A male patient about 85 years old or older; dermoscopy of a skin lesion; recorded as skin type II:
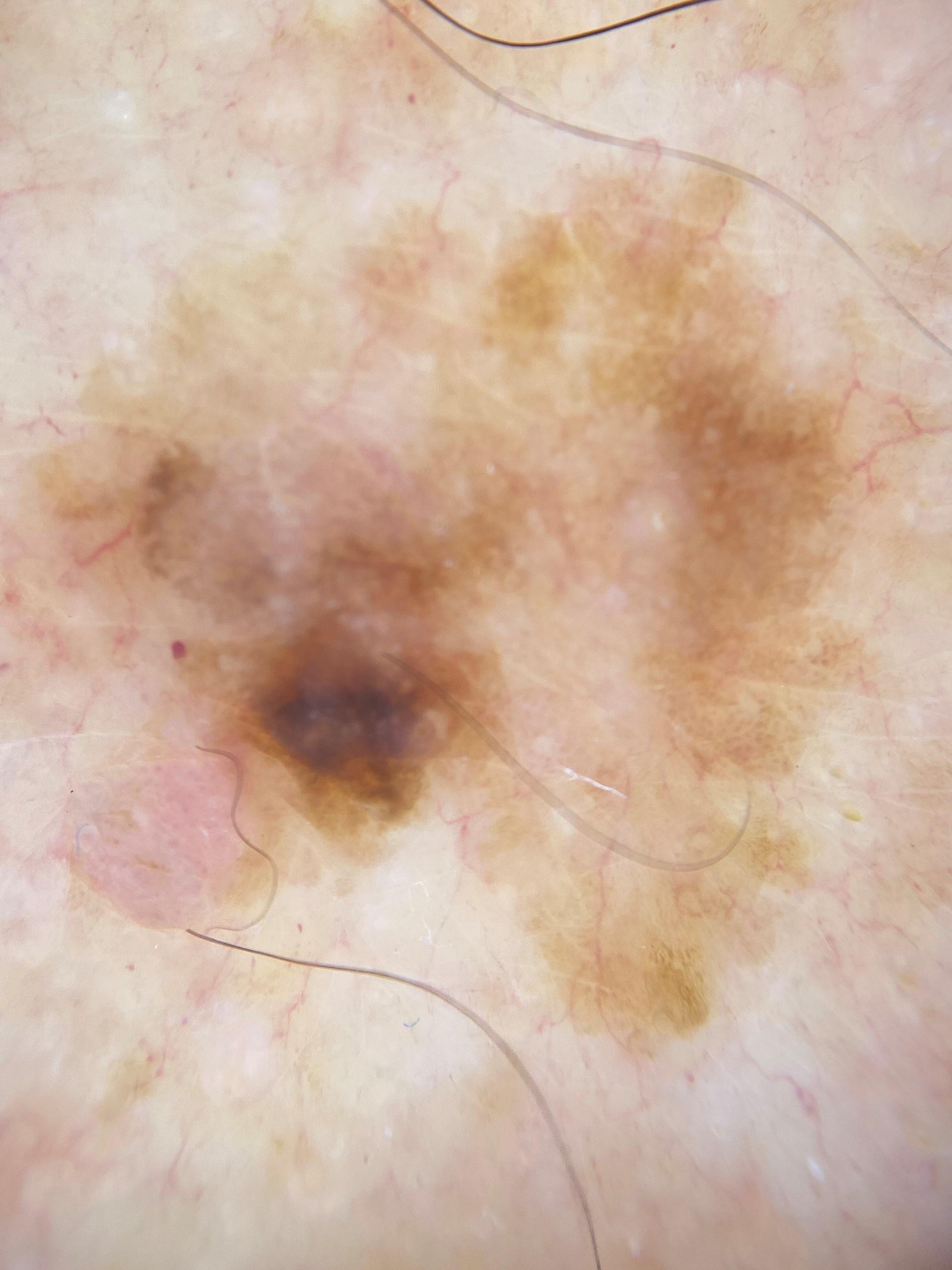site — the trunk | pathology — Seborrheic keratosis (biopsy-proven).